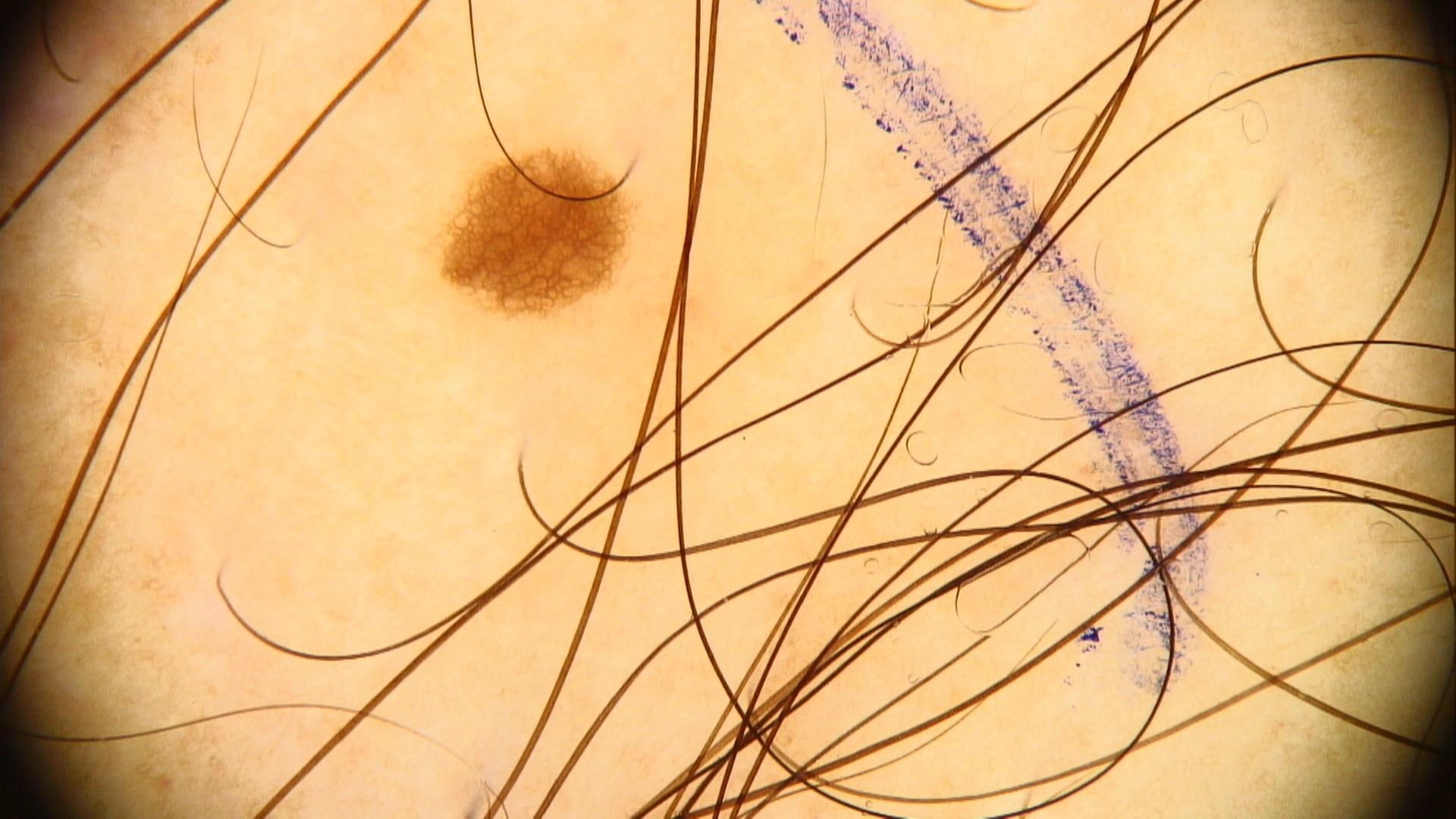Clinical context:
A dermoscopic image of a skin lesion. Located on a lower extremity.
Assessment:
The clinical impression was a benign lesion — a nevus.